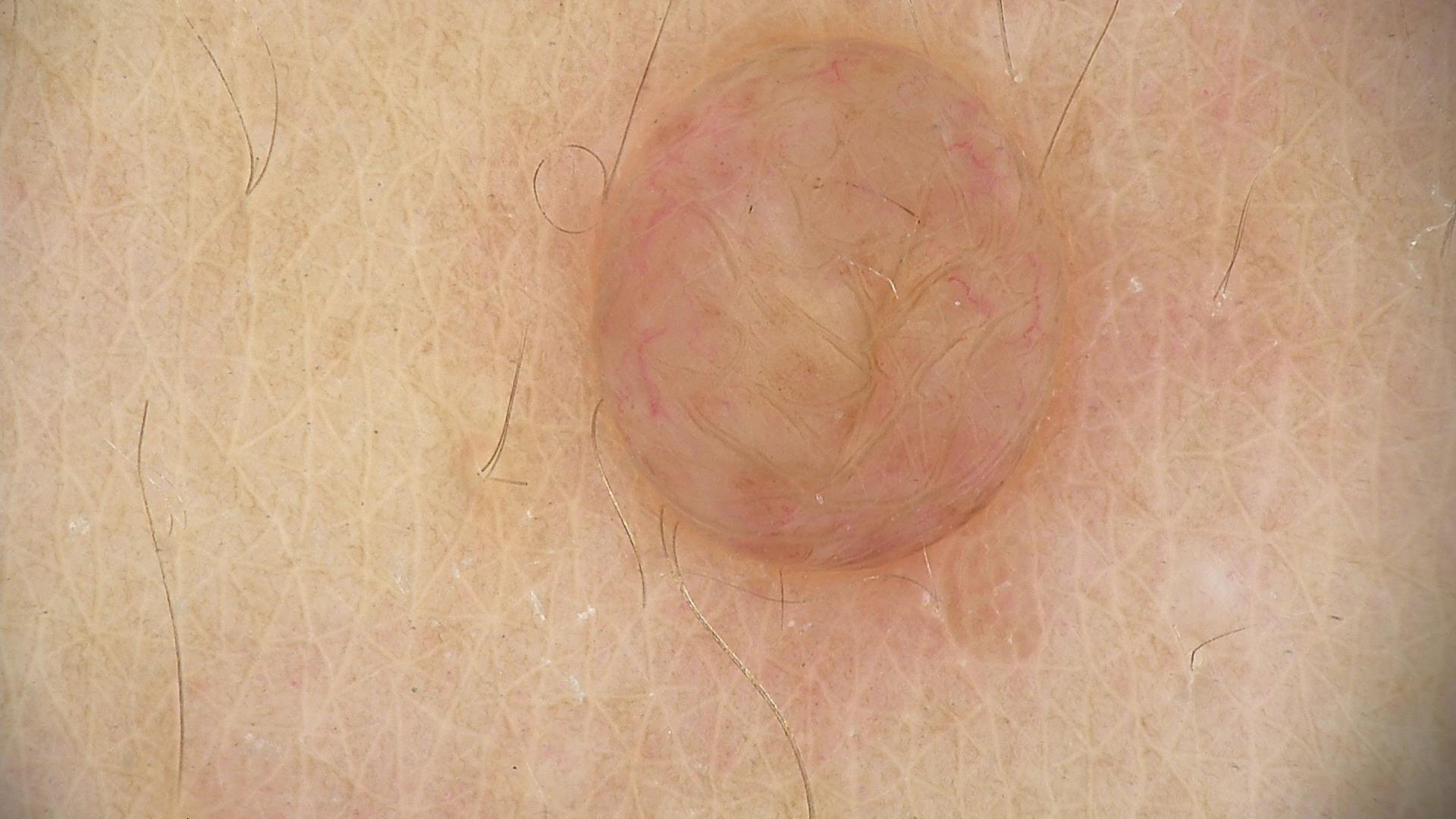Q: What kind of image is this?
A: dermoscopy
Q: What kind of lesion is this?
A: banal
Q: What was the diagnostic impression?
A: dermal nevus (expert consensus)